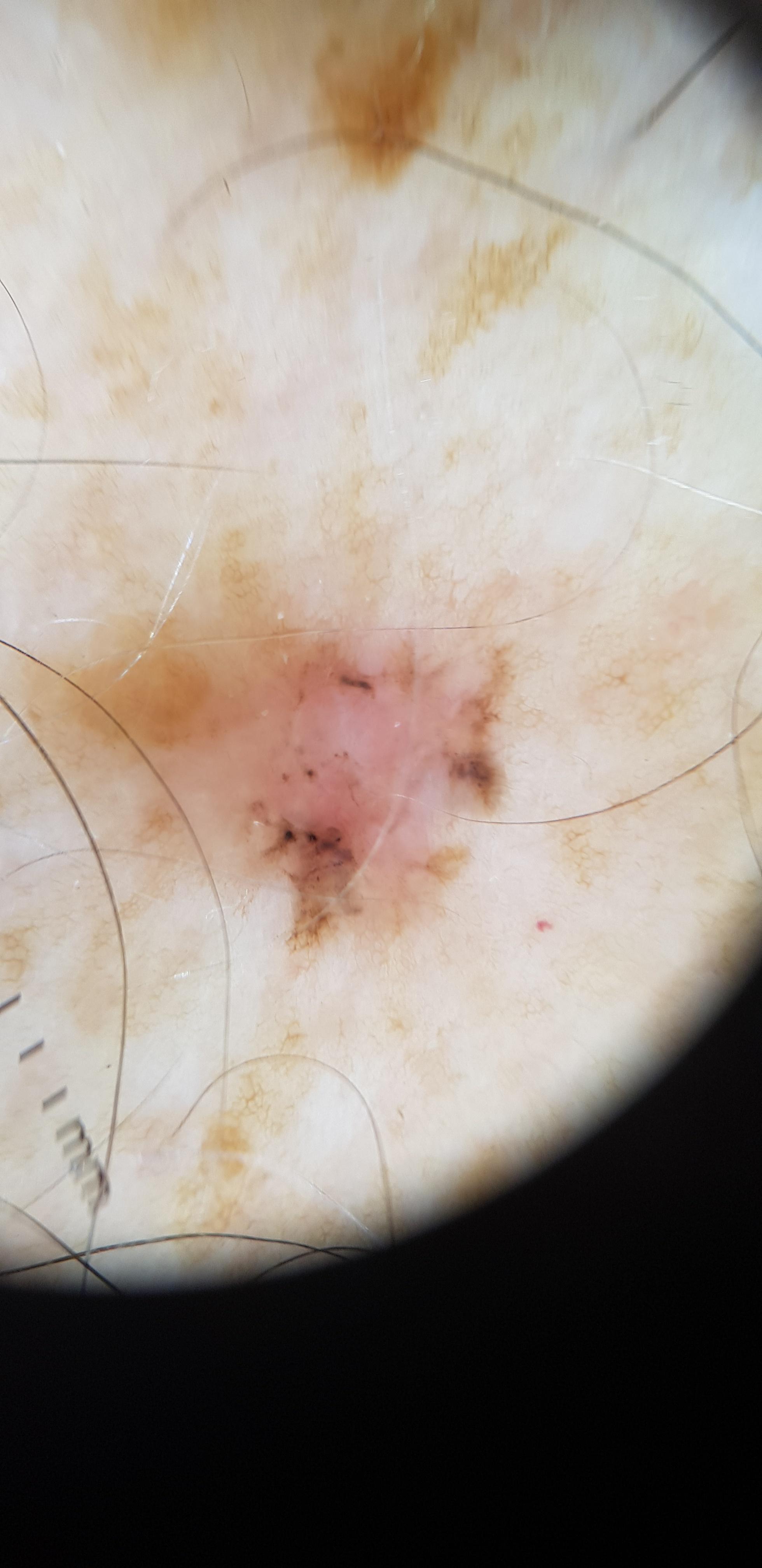A skin lesion imaged with a dermatoscope. Located on the trunk. The biopsy diagnosis was a basal cell carcinoma.